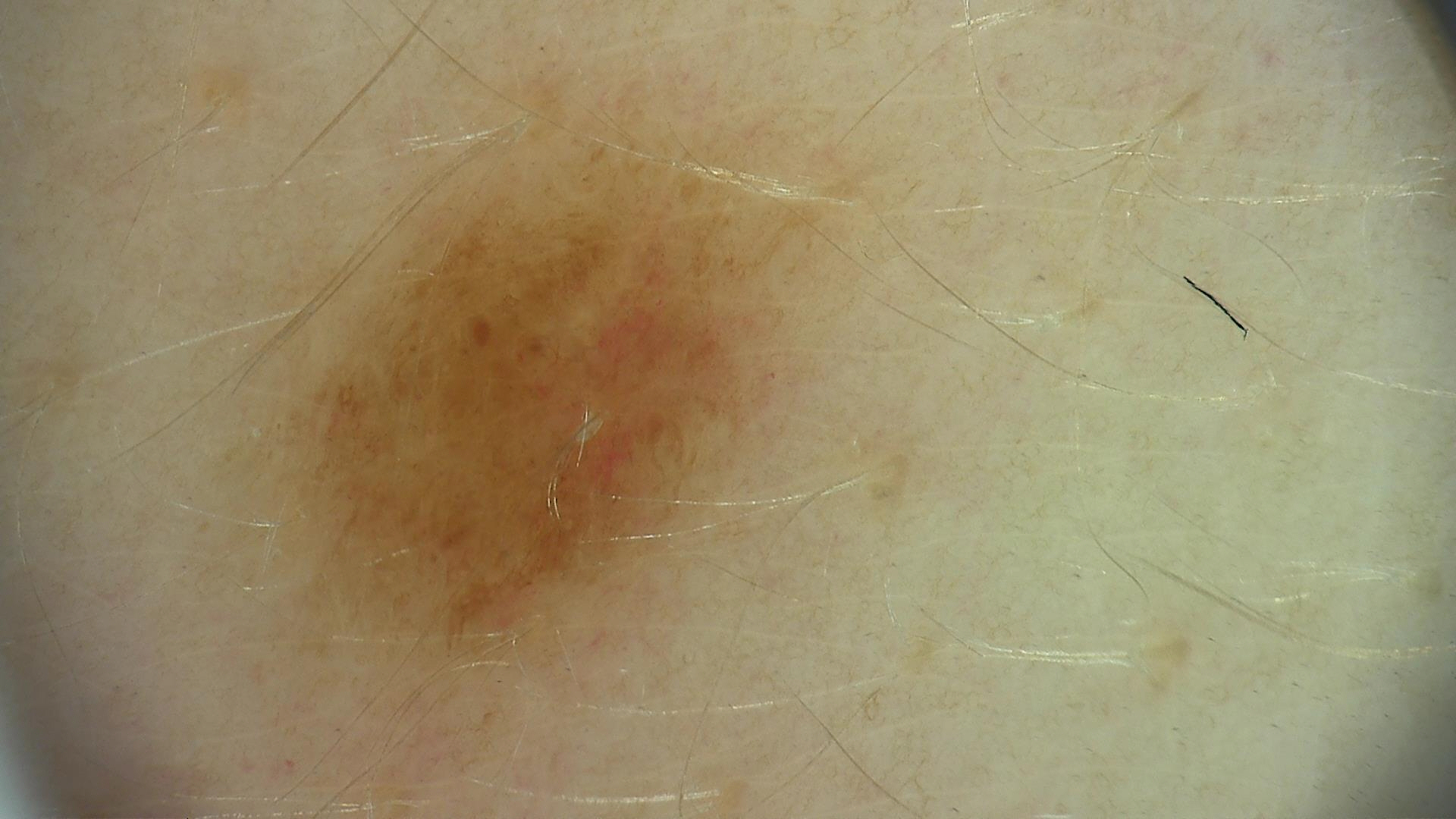Case:
– imaging: dermatoscopy
– assessment: dysplastic junctional nevus (expert consensus)